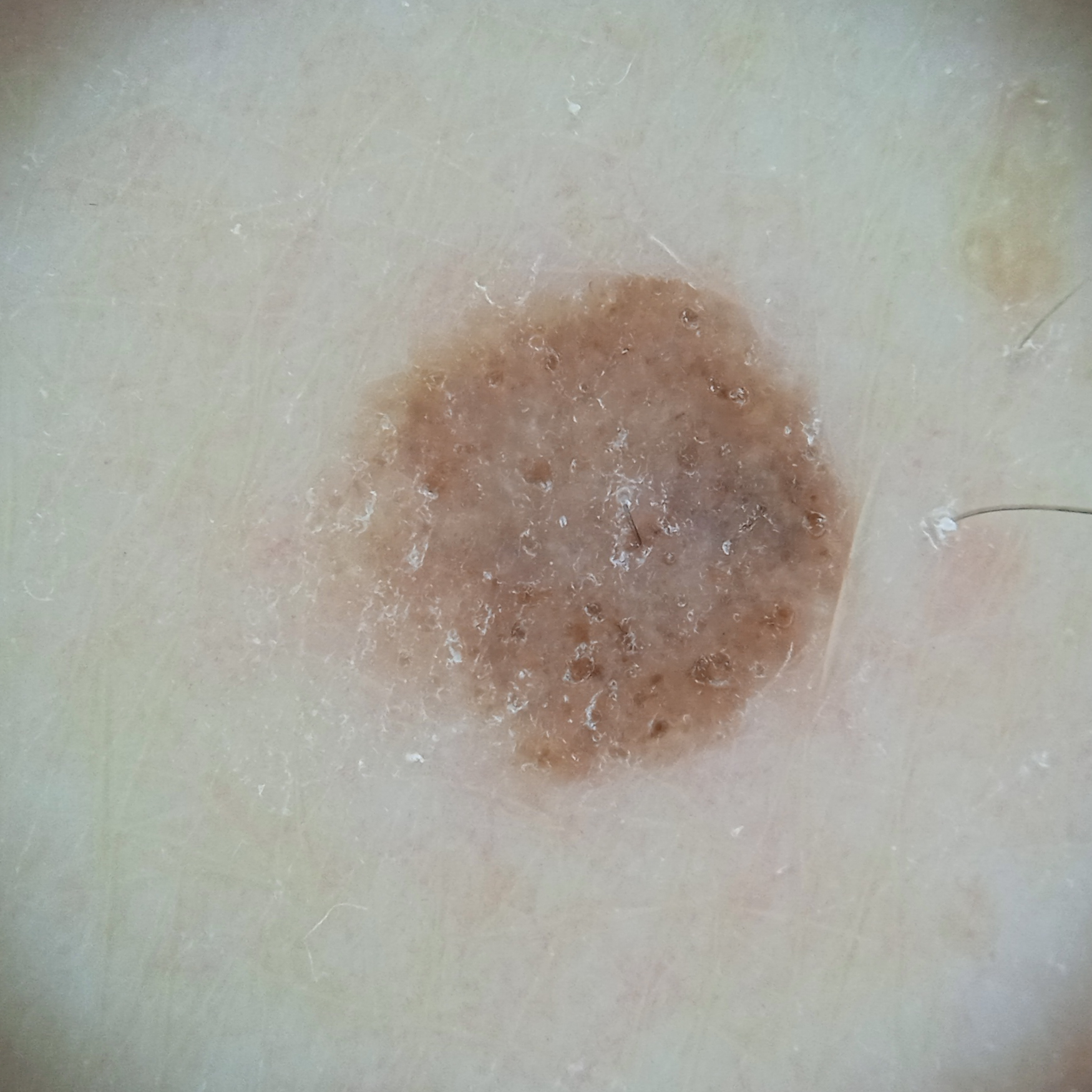A male subject age 79. A dermoscopy image of a skin lesion. The consensus diagnosis for this lesion was a melanocytic nevus.